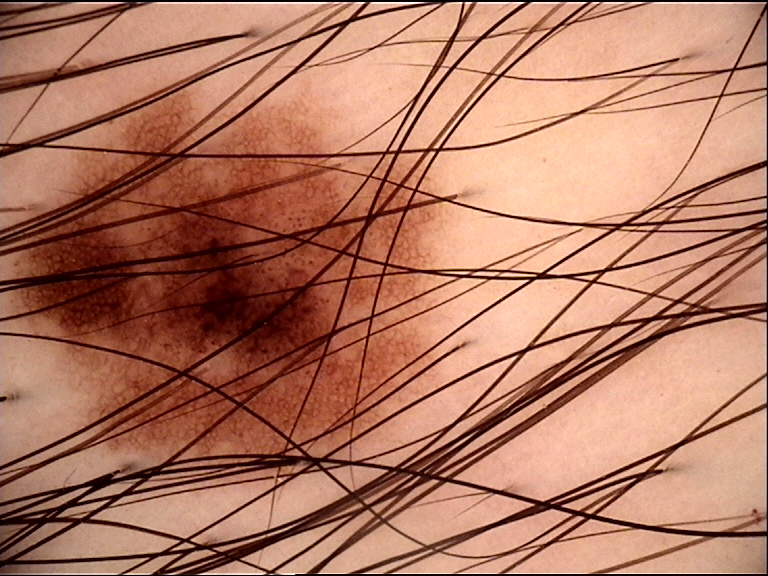A skin lesion imaged with a dermatoscope.
Labeled as a dysplastic junctional nevus.